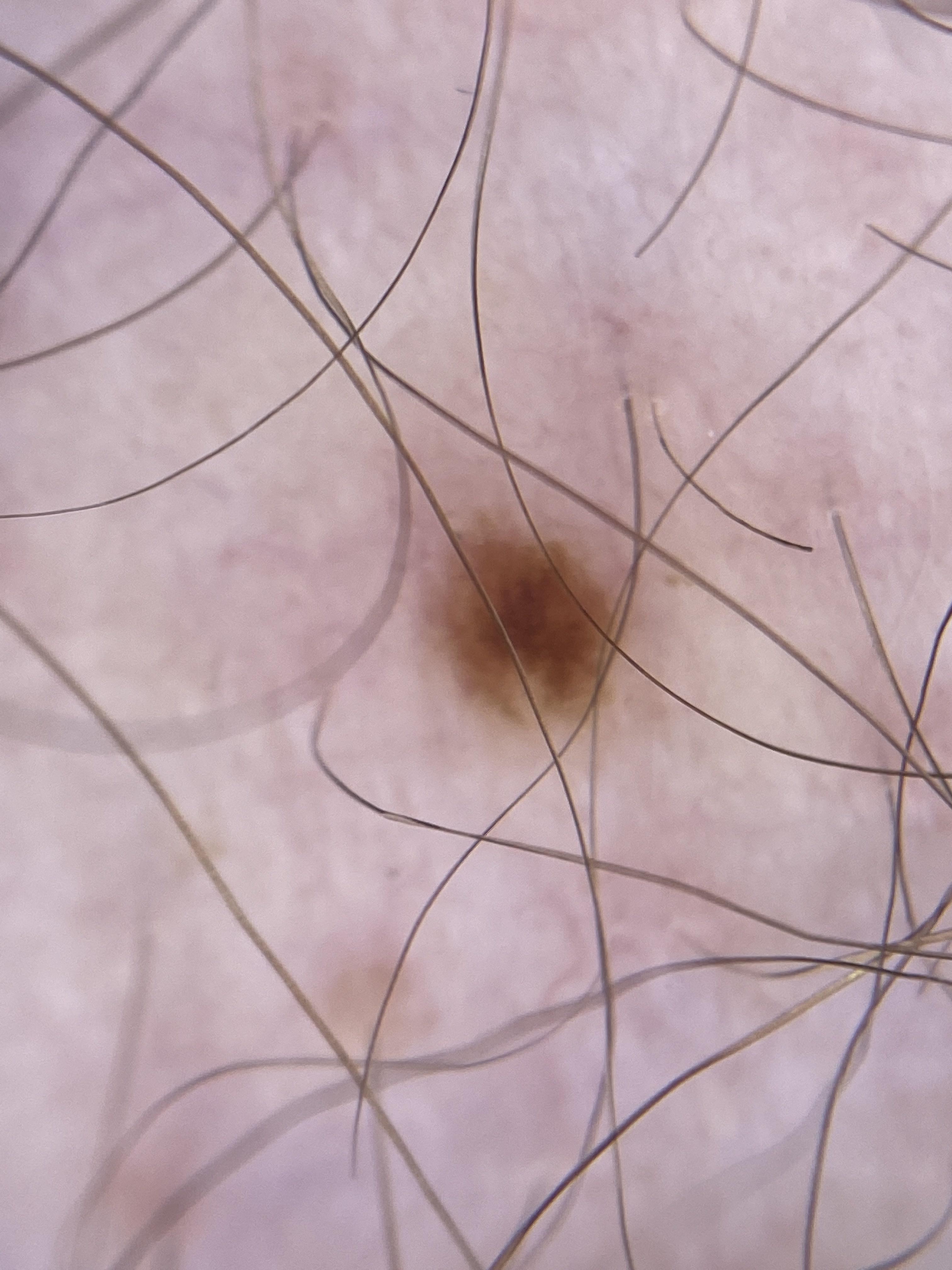Image and clinical context: Dermoscopy of a skin lesion. A male subject aged around 50. Per the chart, a previous melanoma but no first-degree relative with melanoma. The lesion is located on a lower extremity. Assessment: The diagnostic impression was a lesion of melanocytic lineage — a nevus.